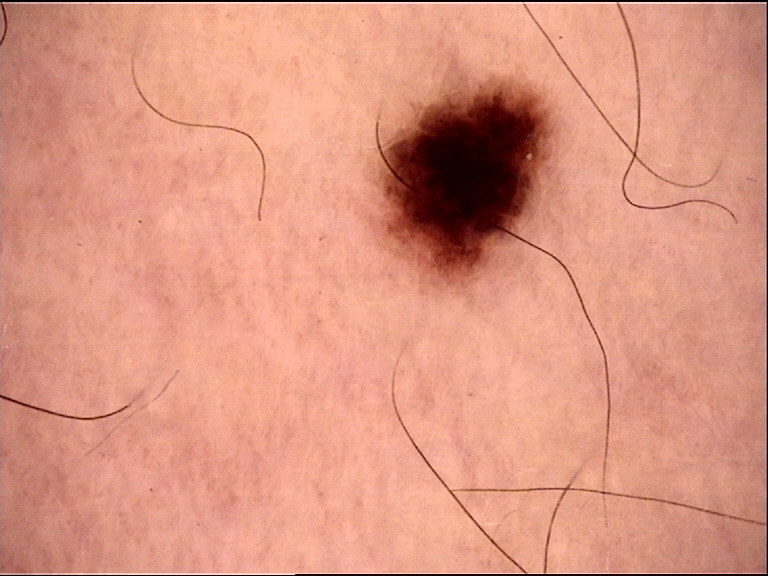Consistent with a junctional nevus.